Present for about one day · skin tone: Fitzpatrick phototype I; human graders estimated 2 on the Monk skin tone scale · the subject is 18–29, female · the lesion is described as flat and raised or bumpy · the arm is involved · no constitutional symptoms were reported · the photo was captured at an angle · symptoms reported: itching · self-categorized by the patient as a rash — 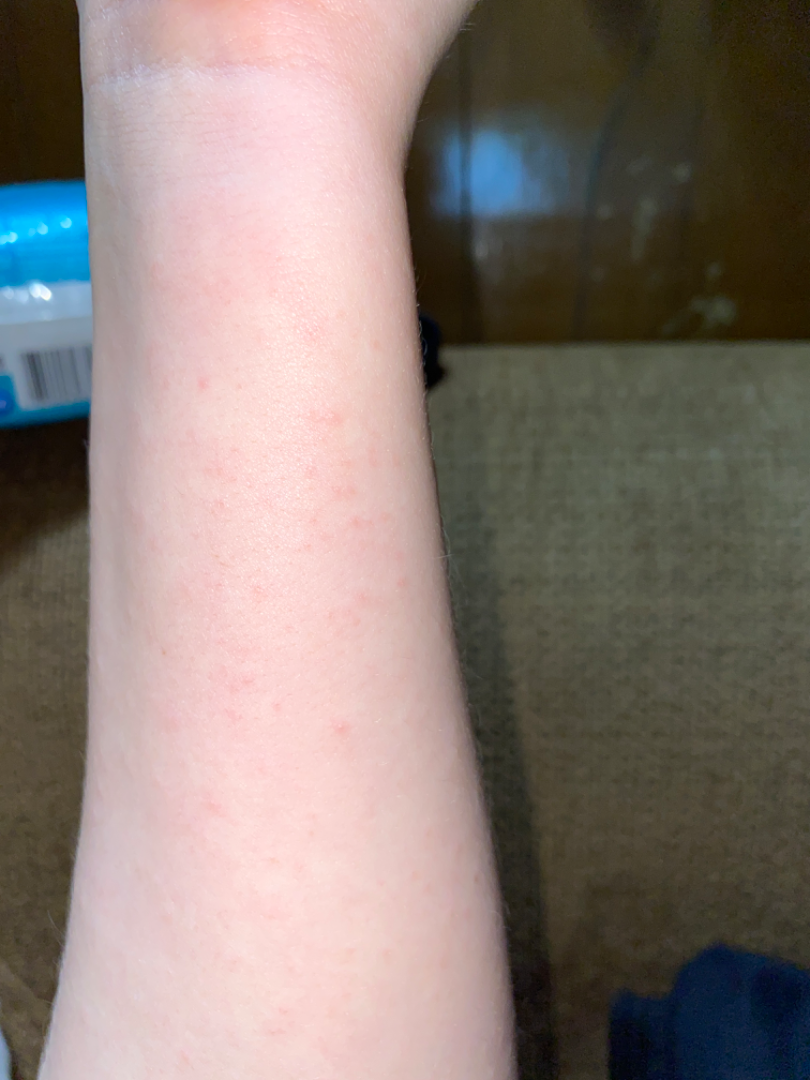The condition could not be reliably identified from the image.